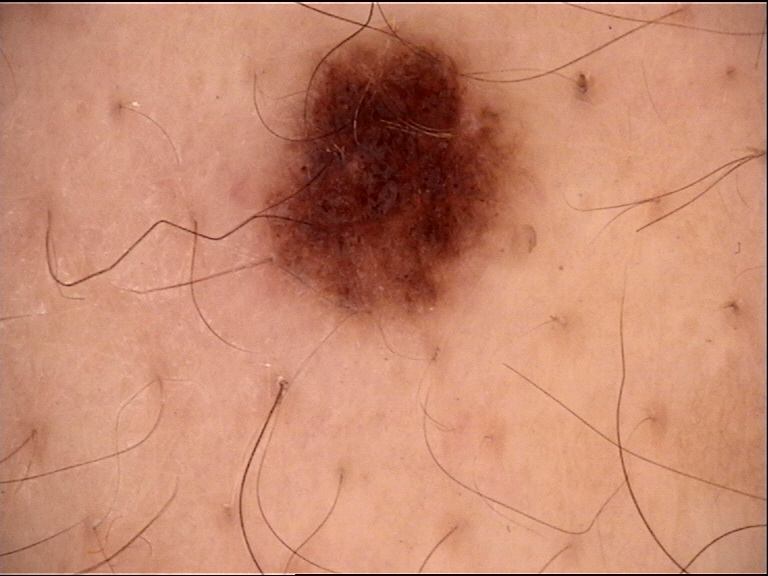The diagnosis was a dysplastic junctional nevus.